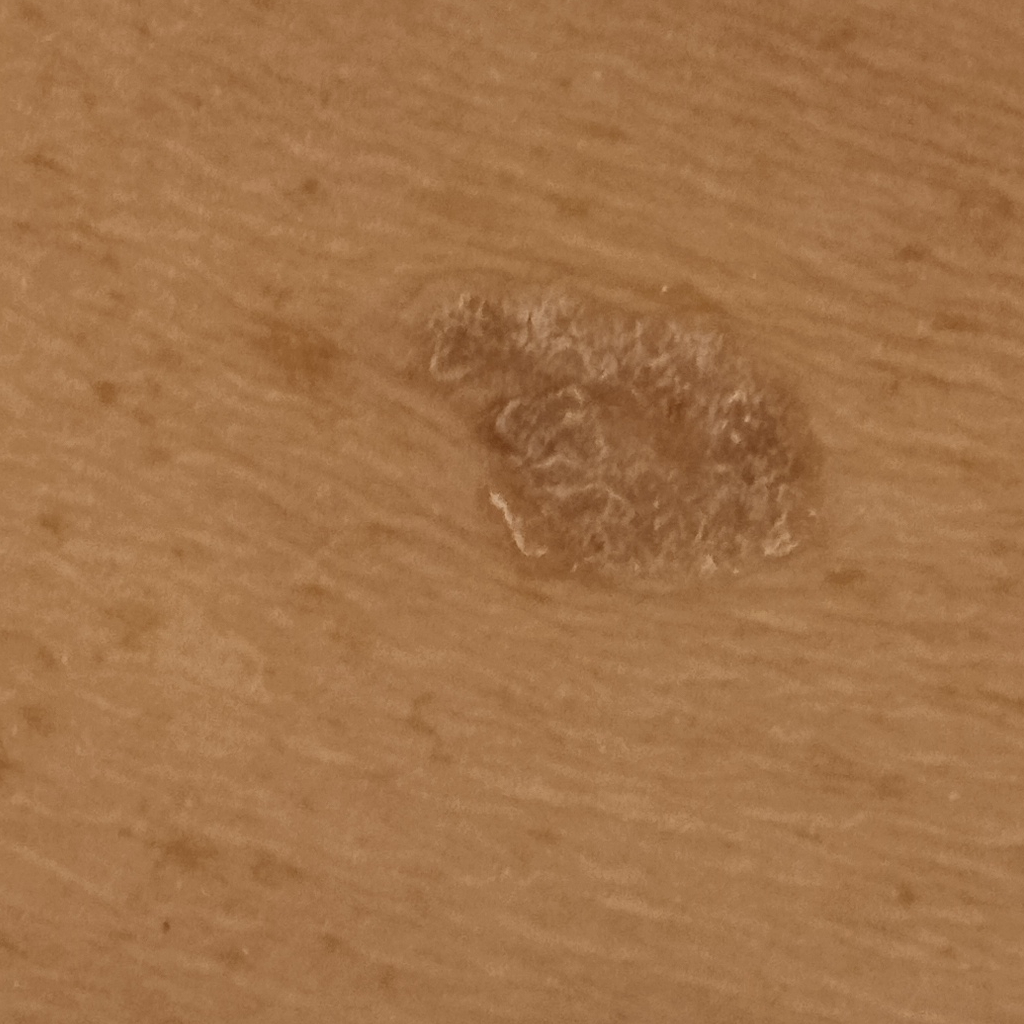nevus count: few melanocytic nevi overall, clinical context: research study (no referral diagnosis), image type: clinical photograph, sun reaction: skin reddens with sun exposure, risk factors: a personal history of cancer, anatomic site: the back, diameter: 16.5 mm, diagnostic label: seborrheic keratosis (dermatologist consensus).